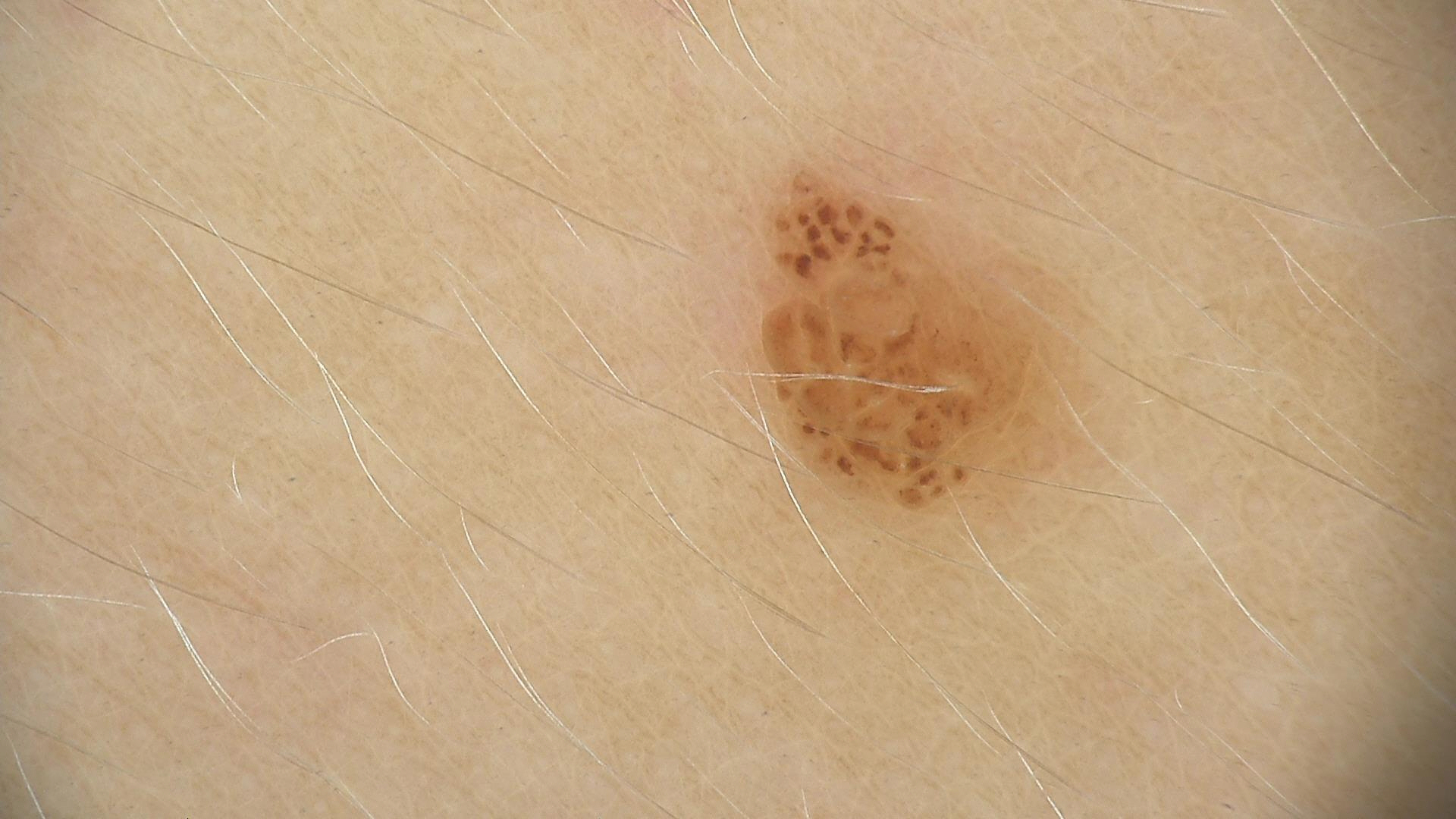A dermatoscopic image of a skin lesion.
This is a banal lesion.
The diagnosis was a compound nevus.